The subject is a female aged 50–59. The photograph was taken at an angle. Located on the leg: 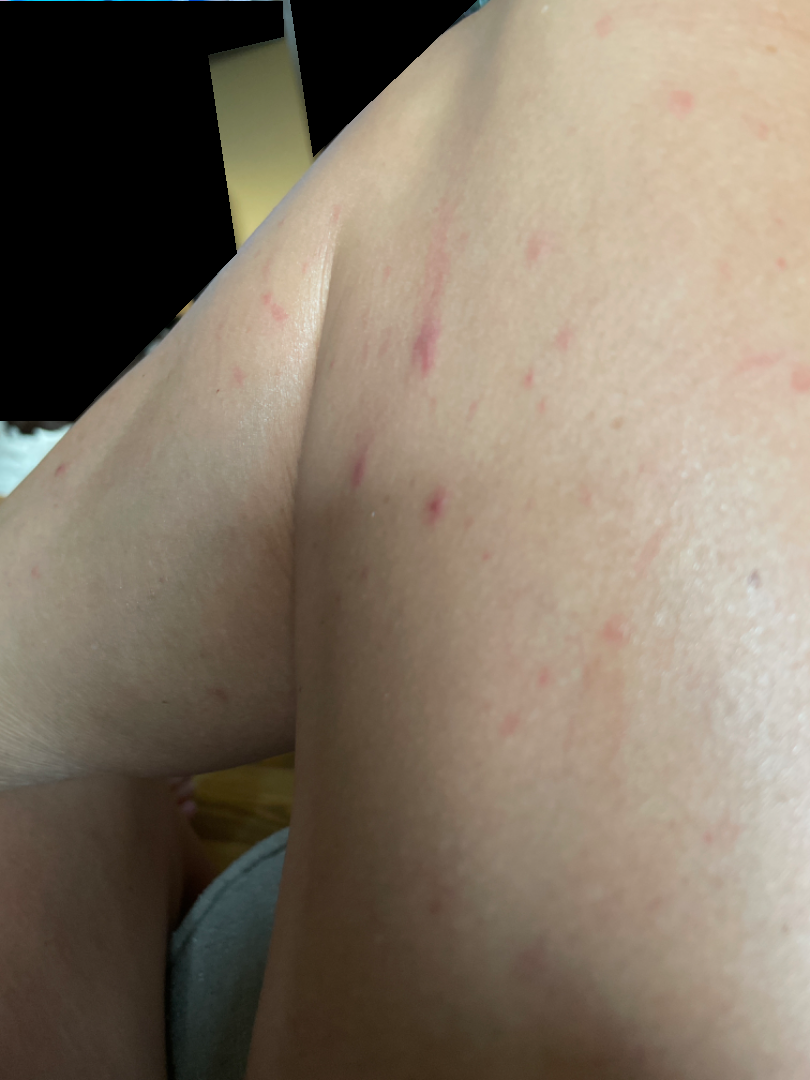present for=about one day
other reported symptoms=none reported
lesion texture=flat
lesion symptoms=bothersome appearance
patient describes the issue as=a rash
clinical impression=Folliculitis (primary); Insect Bite (remote); Viral Exanthem (remote)